A female subject age 50. Collected as part of a research study, without a referral diagnosis: 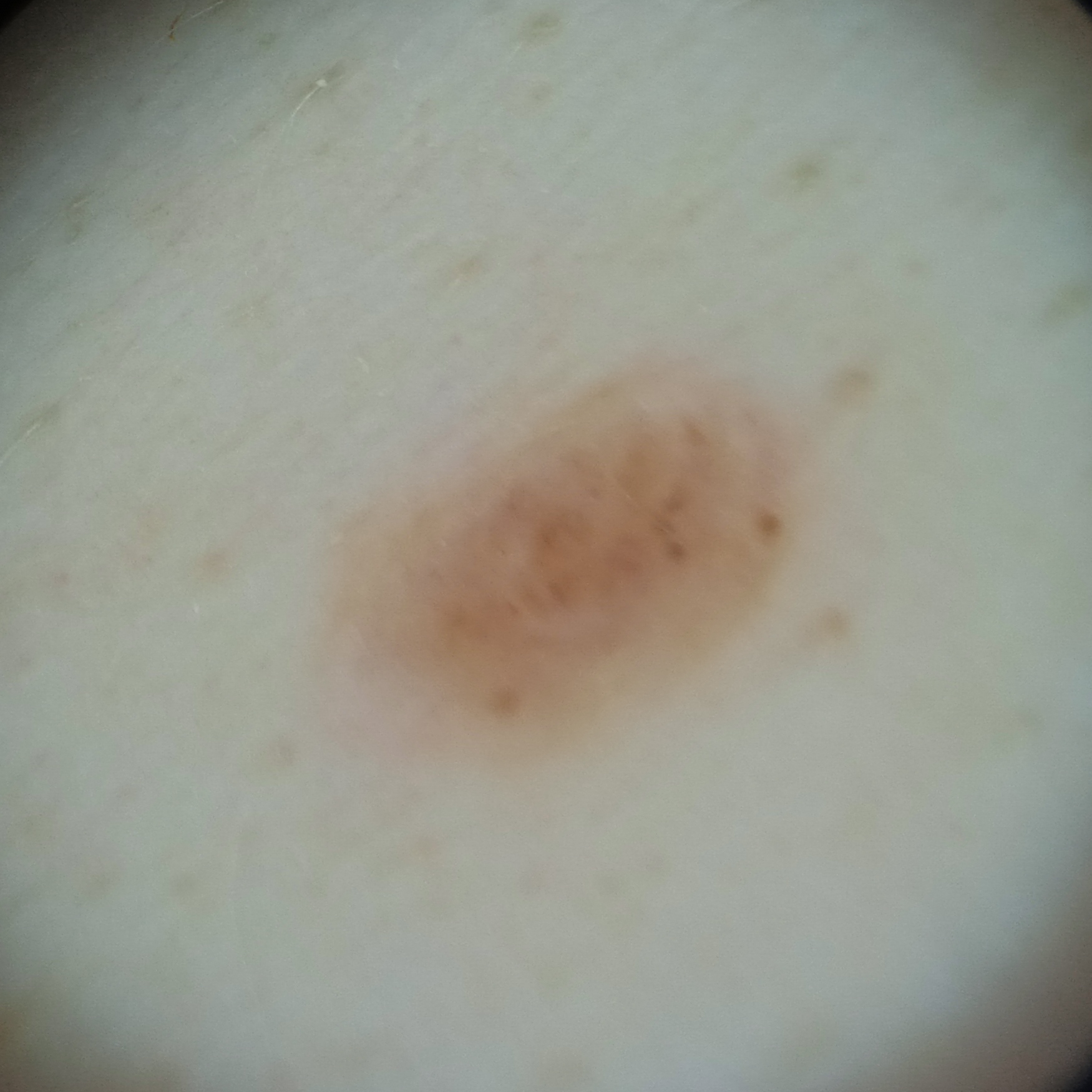The lesion is on the torso. The lesion measures approximately 4.9 mm. The lesion was assessed as a melanocytic nevus.